A dermoscopic close-up of a skin lesion:
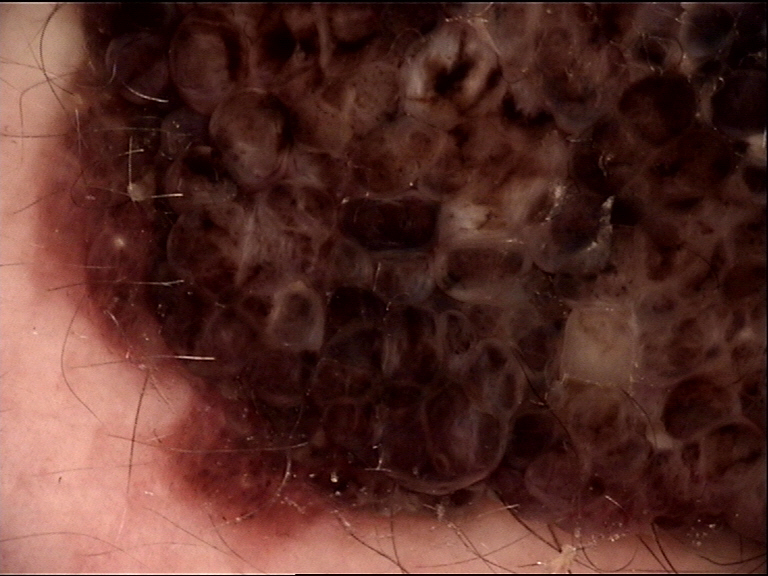<lesion>
<diagnosis>
<name>congenital compound nevus</name>
<code>ccb</code>
<malignancy>benign</malignancy>
<super_class>melanocytic</super_class>
<confirmation>expert consensus</confirmation>
</diagnosis>
</lesion>